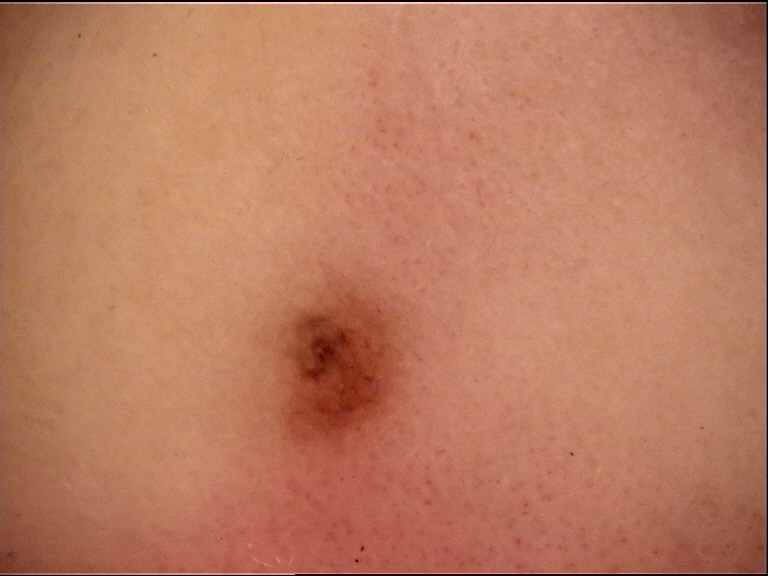diagnosis — dysplastic compound nevus (expert consensus)